Female contributor, age 50–59 · the photograph was taken at an angle.
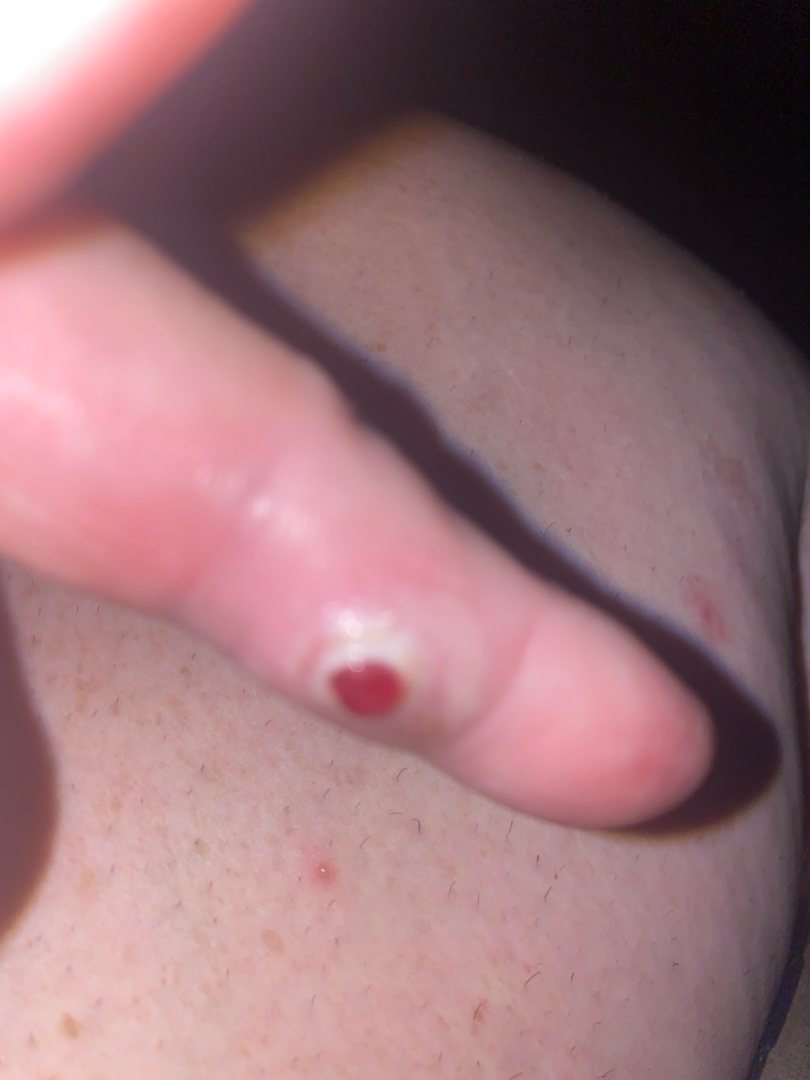symptoms=bleeding
history=one to three months
impression=most consistent with Pyogenic granuloma; also on the differential is Melanoma